The head or neck is involved, this image was taken at an angle:
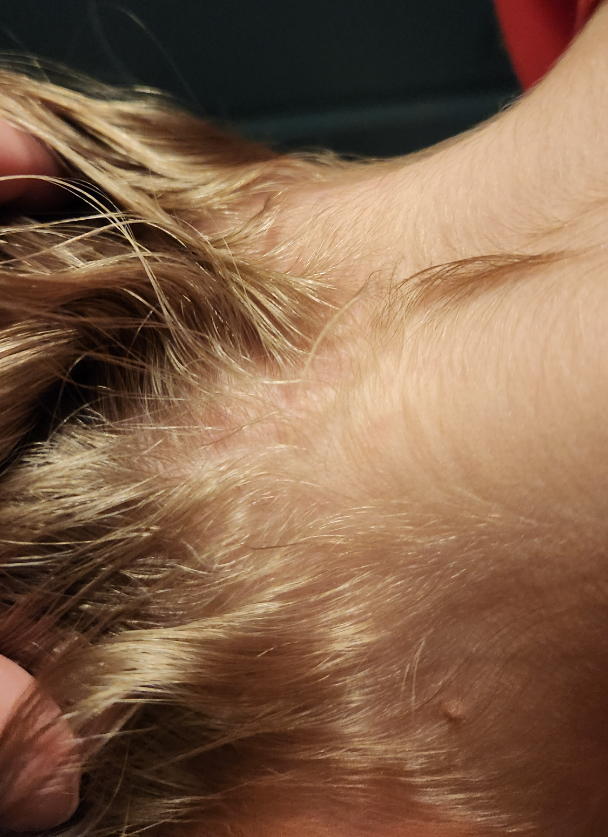assessment = not assessable.